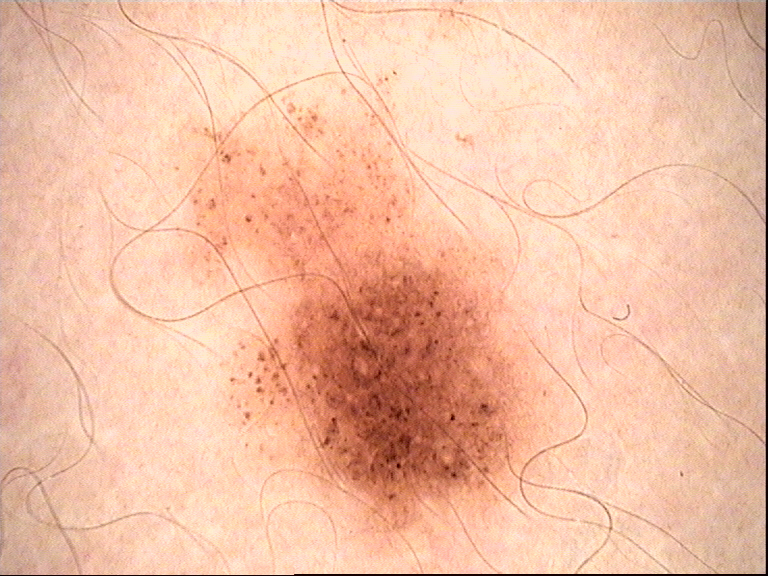Impression: Diagnosed as a benign lesion — a dysplastic junctional nevus.